A dermoscopic photograph of a skin lesion.
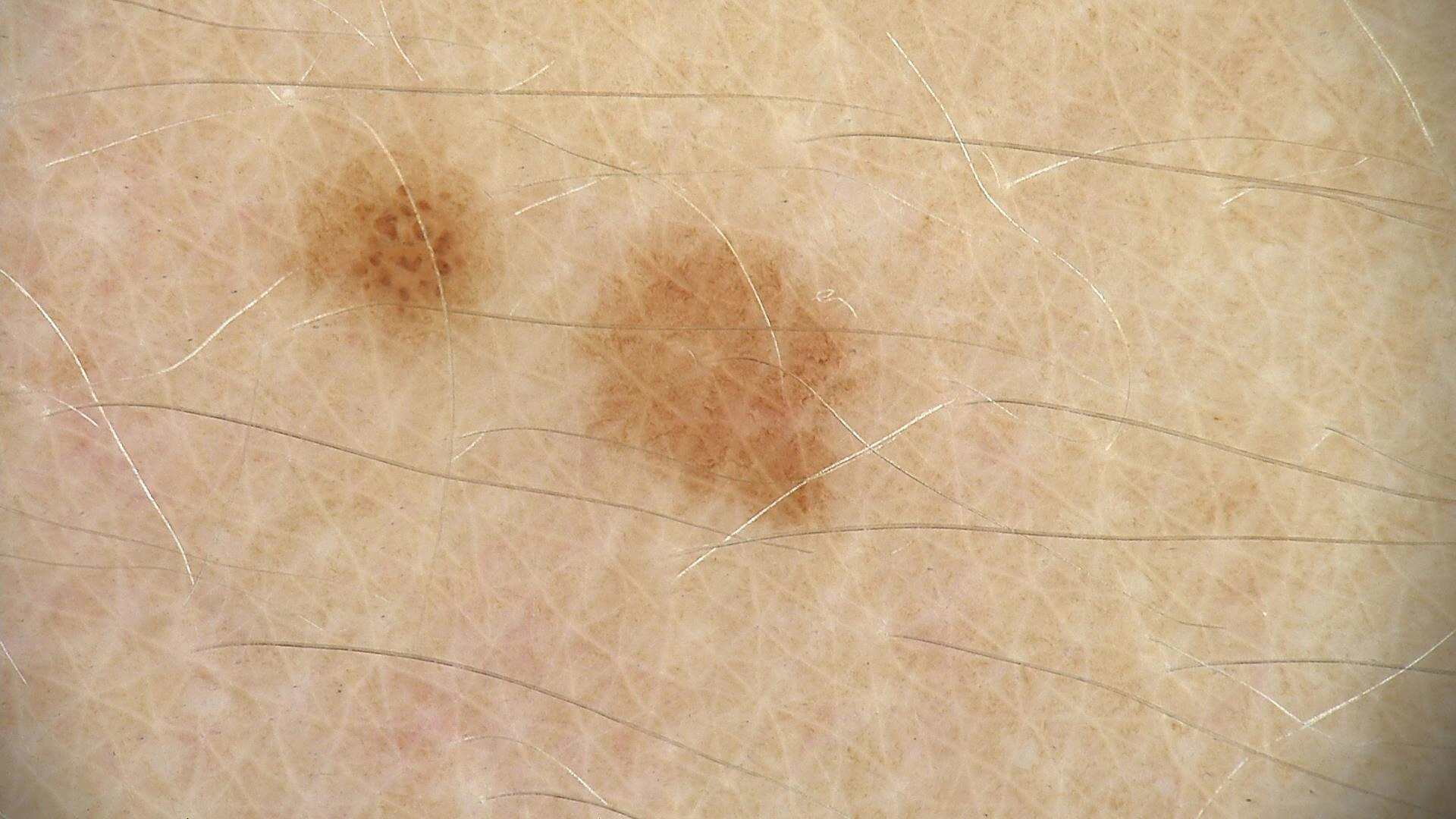diagnostic label: dysplastic junctional nevus (expert consensus).